The lesion involves the leg, front of the torso, top or side of the foot and back of the torso. An image taken at an angle. The subject is female:
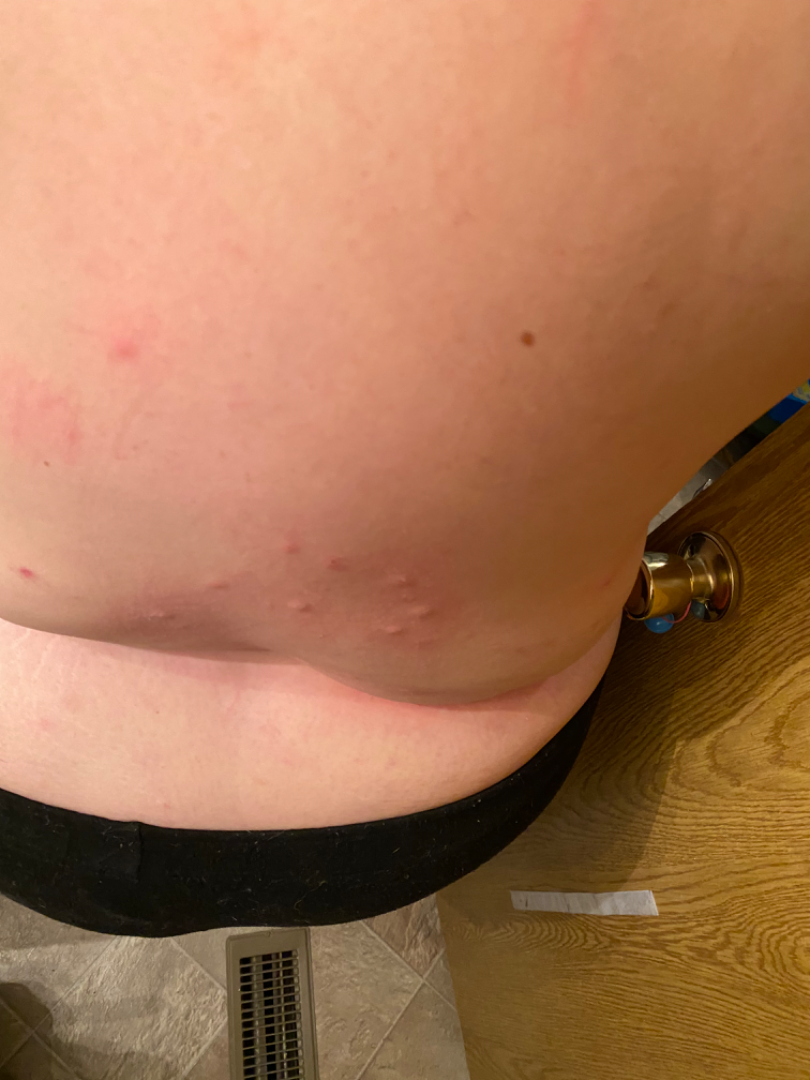The reviewing dermatologist was unable to assign a differential diagnosis from the image.
The patient considered this a rash.
Reported lesion symptoms include itching and burning.
Reported duration is one to four weeks.
Texture is reported as fluid-filled and raised or bumpy.